A dermatoscopic image of a skin lesion:
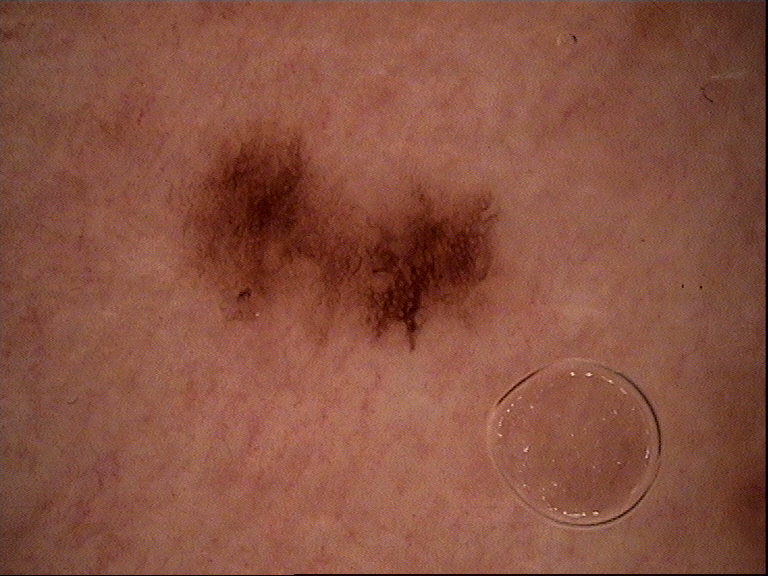diagnosis = dysplastic junctional nevus (expert consensus).